The photograph was taken at a distance · reported lesion symptoms include pain, darkening, burning, itching, bleeding and enlargement · the lesion is described as fluid-filled · the patient indicates associated fatigue and joint pain · the lesion involves the front of the torso · the patient considered this a rash — 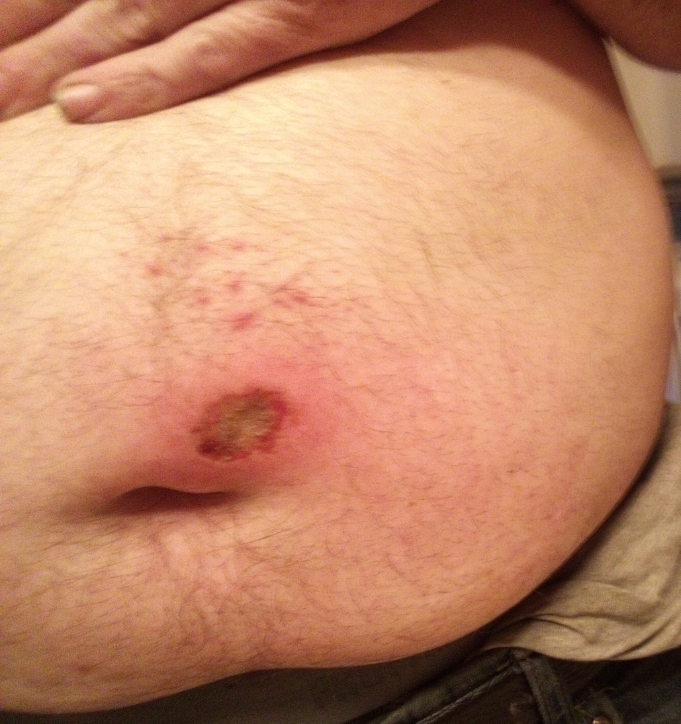The reviewing dermatologist was unable to assign a differential diagnosis from the image.